A dermoscopy image of a single skin lesion.
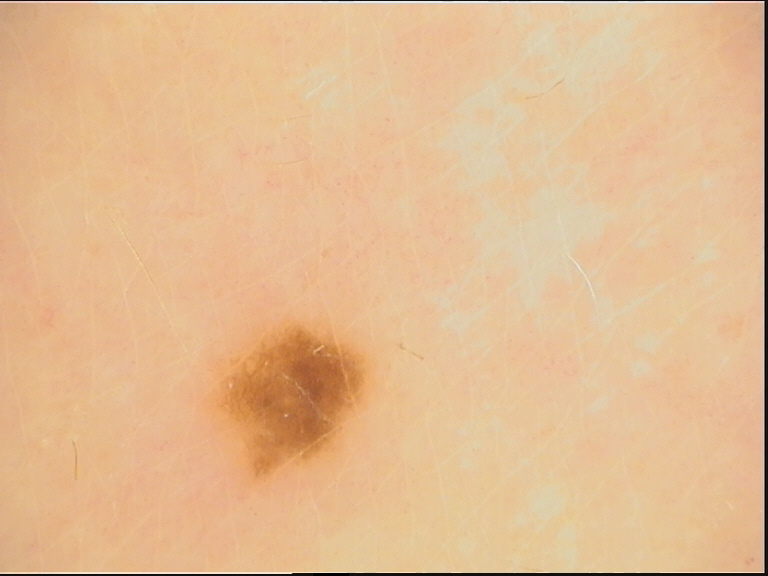Findings:
* subtype: banal
* class: junctional nevus (expert consensus)